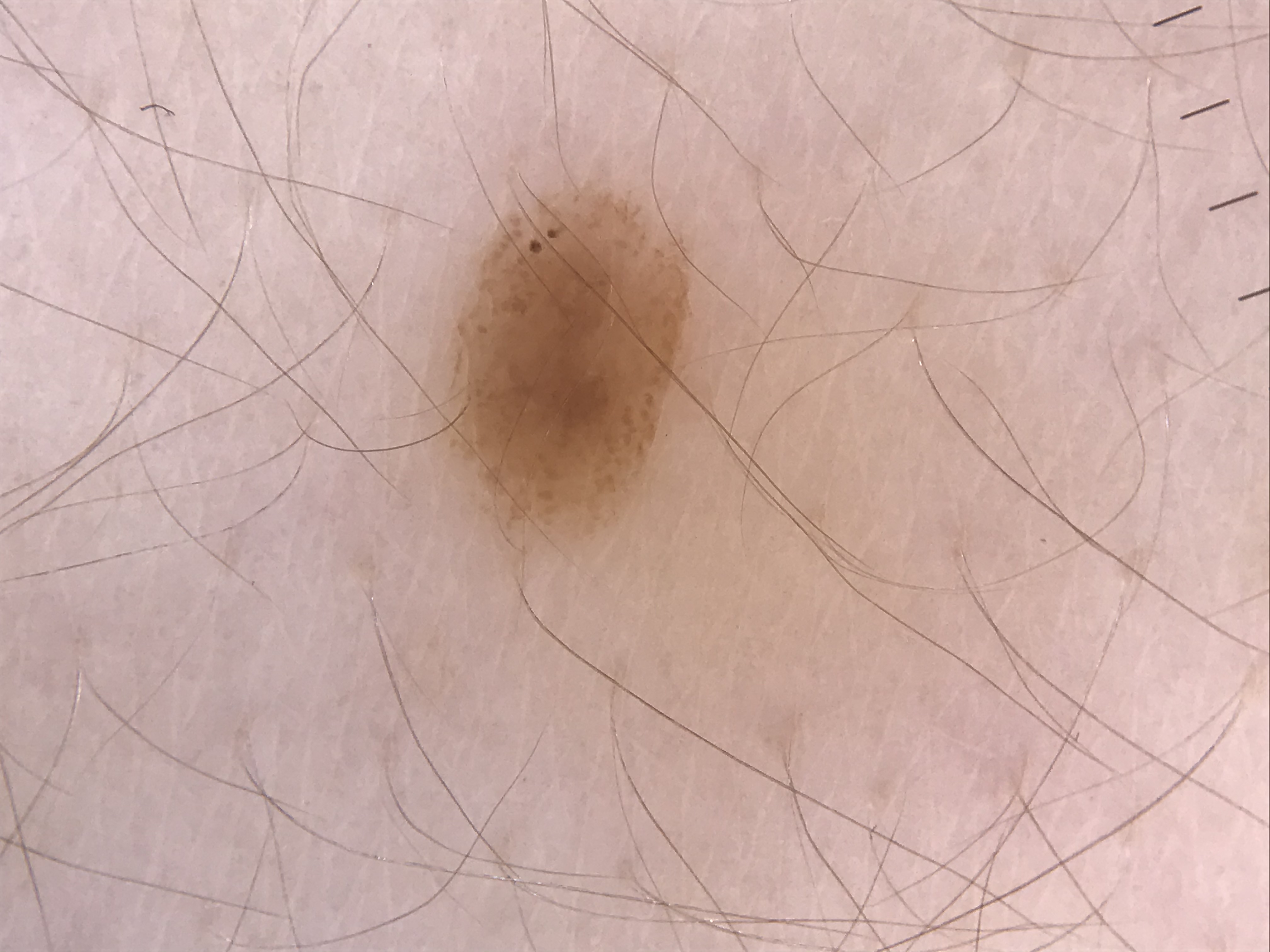A dermatoscopic image of a skin lesion. Labeled as a dysplastic junctional nevus.